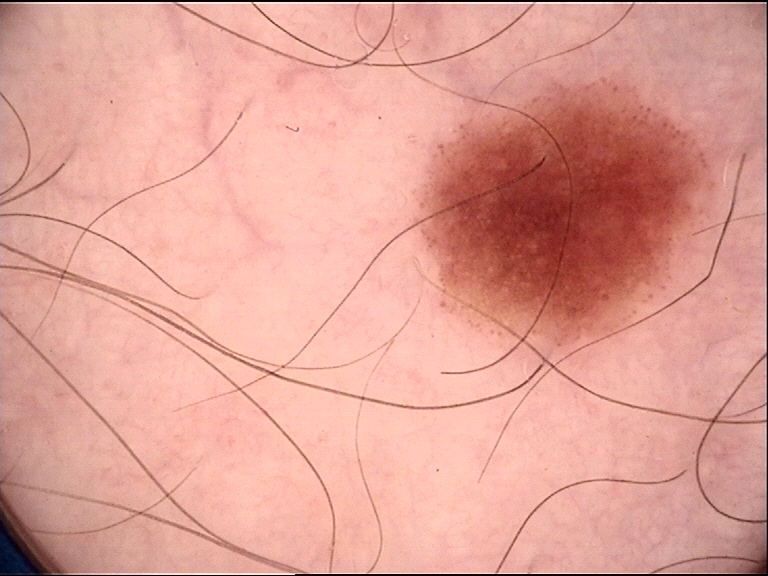{
  "image": "dermatoscopy",
  "diagnosis": {
    "name": "dysplastic junctional nevus",
    "code": "jd",
    "malignancy": "benign",
    "super_class": "melanocytic",
    "confirmation": "expert consensus"
  }
}